By history, no tobacco use · the patient was assessed as FST II · a female subject 73 years of age.
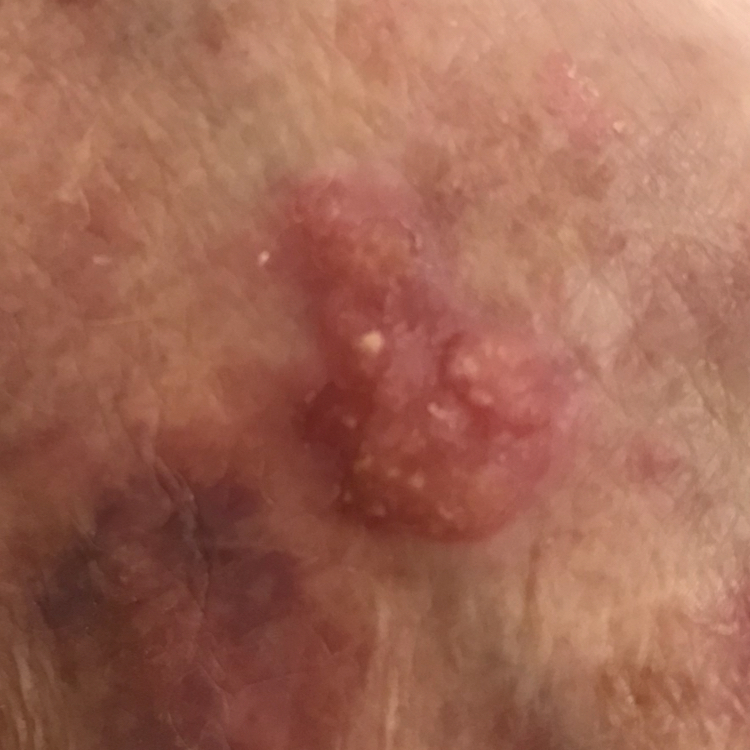The lesion was found on a hand. The lesion measures 18 × 14 mm. By the patient's account, the lesion itches and is elevated. Biopsy-confirmed as a malignancy — a squamous cell carcinoma.